A skin lesion imaged with a dermatoscope · Fitzpatrick III · the chart notes no previous melanoma and no melanoma in first-degree relatives · a male subject in their 70s: 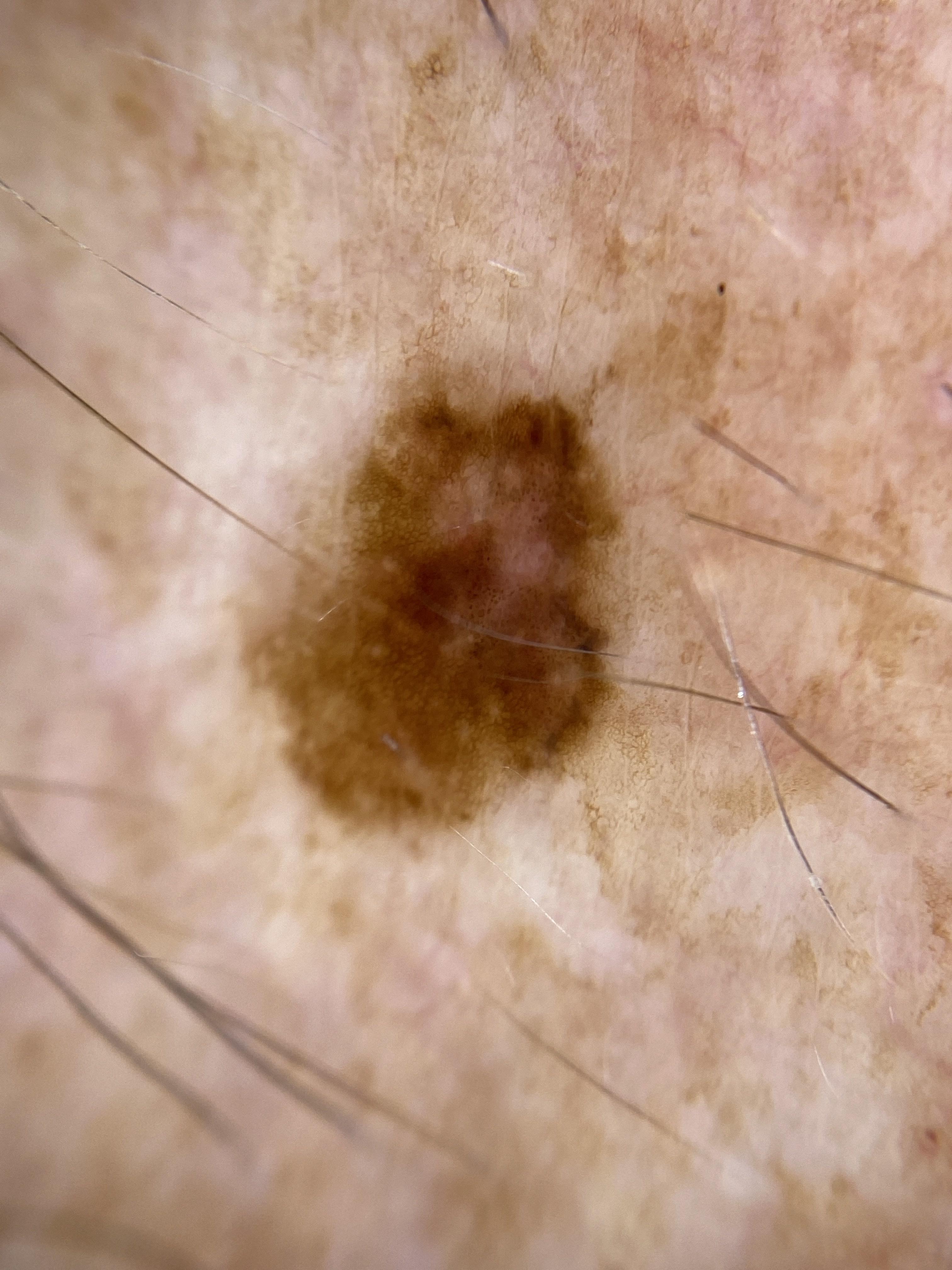diagnosis: Melanoma (biopsy-proven).